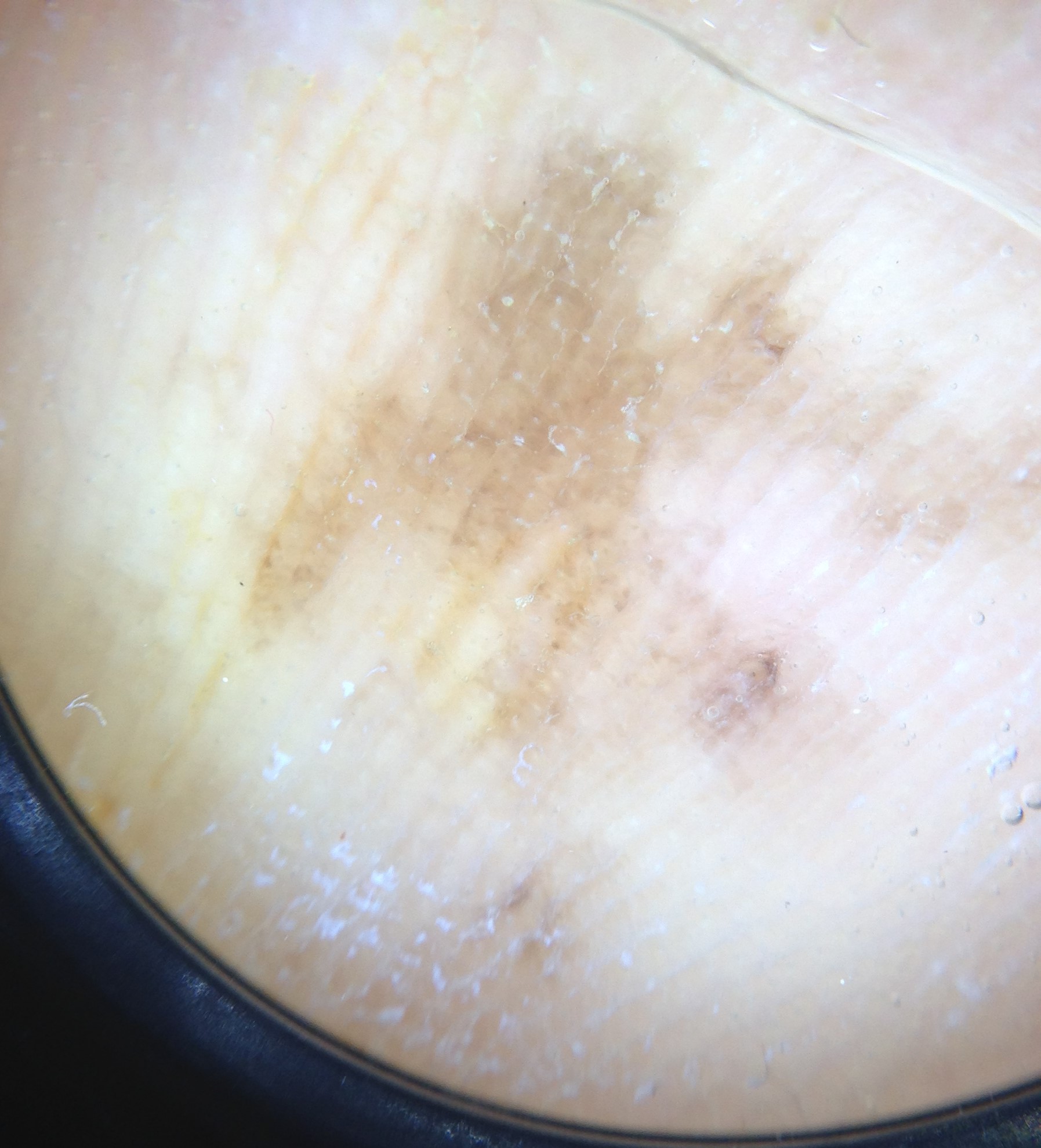A dermoscopy image of a single skin lesion. The biopsy diagnosis was a skin cancer — an acral lentiginous melanoma.